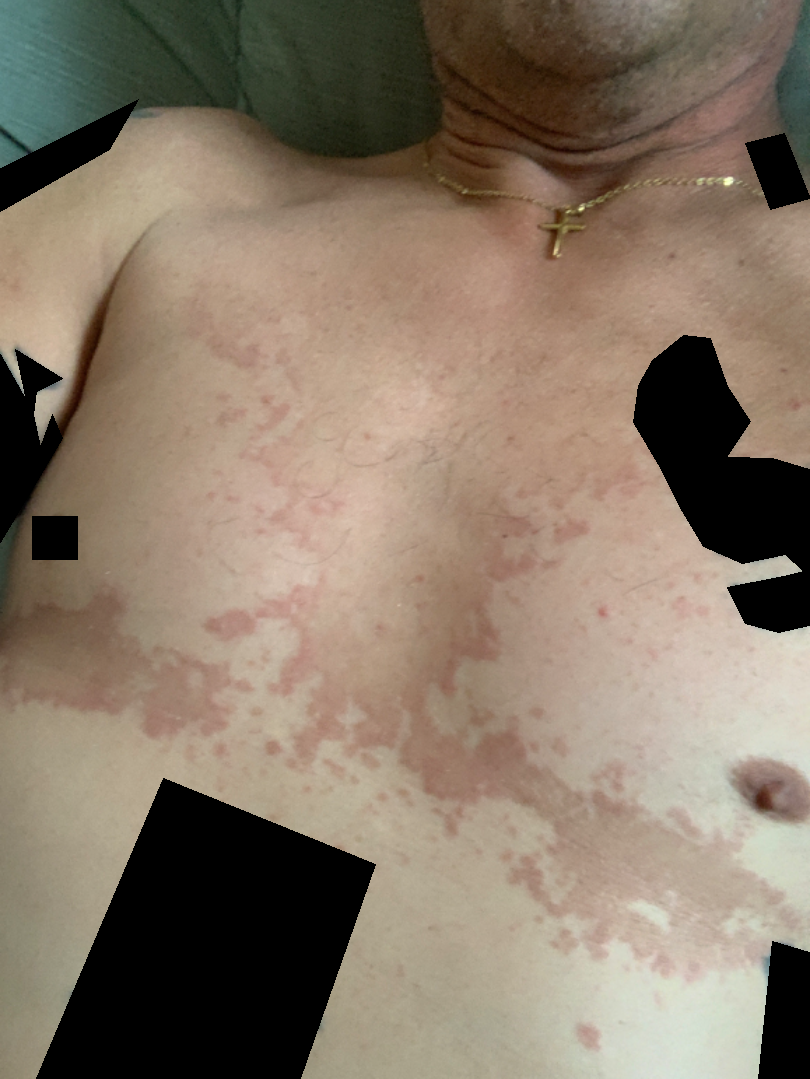assessment = Tinea Versicolor (primary); Confluent and reticulate papillomatosis (considered).